This image was taken at a distance; the arm, back of the hand and back of the torso are involved; female patient, age 30–39; reported duration is about one day; the patient considered this a rash; no constitutional symptoms were reported; the patient notes itching; texture is reported as raised or bumpy: 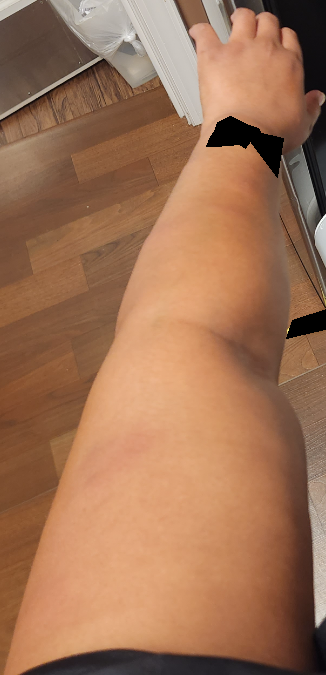Case summary:
* impression: Cutaneous lupus (most likely); Urticaria (considered)